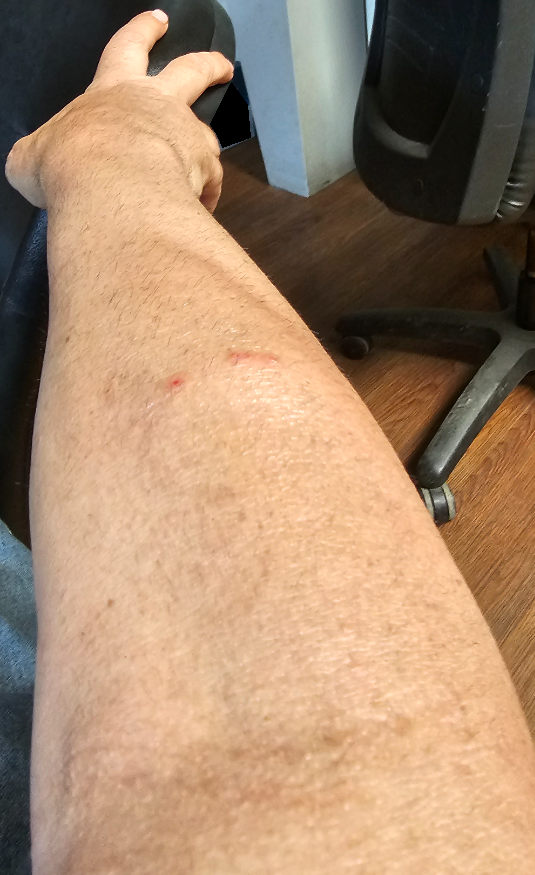Clinical context: The patient described the issue as a rash. The arm is involved. Reported duration is less than one week. Skin tone: FST V. The photo was captured at an angle. Assessment: On remote dermatologist review: the differential, in no particular order, includes Impetigo and Allergic Contact Dermatitis.